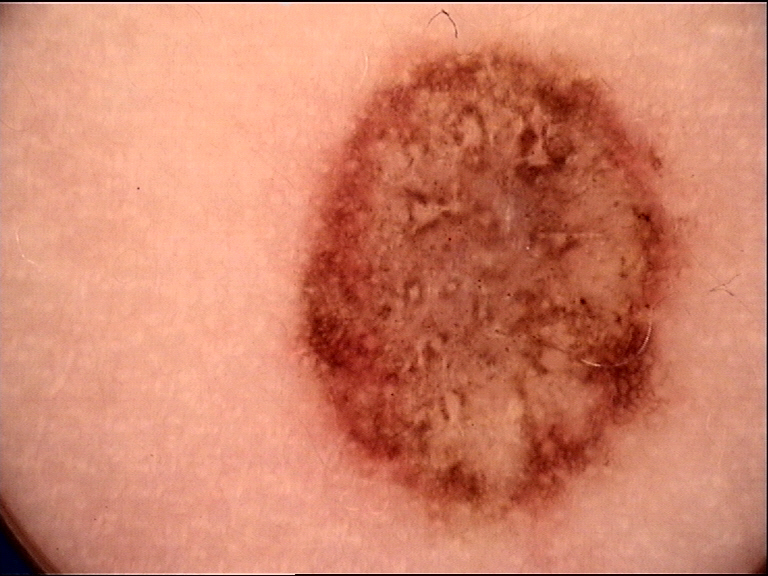A dermoscopic close-up of a skin lesion. The morphology is that of a banal lesion. Labeled as a congenital compound nevus.